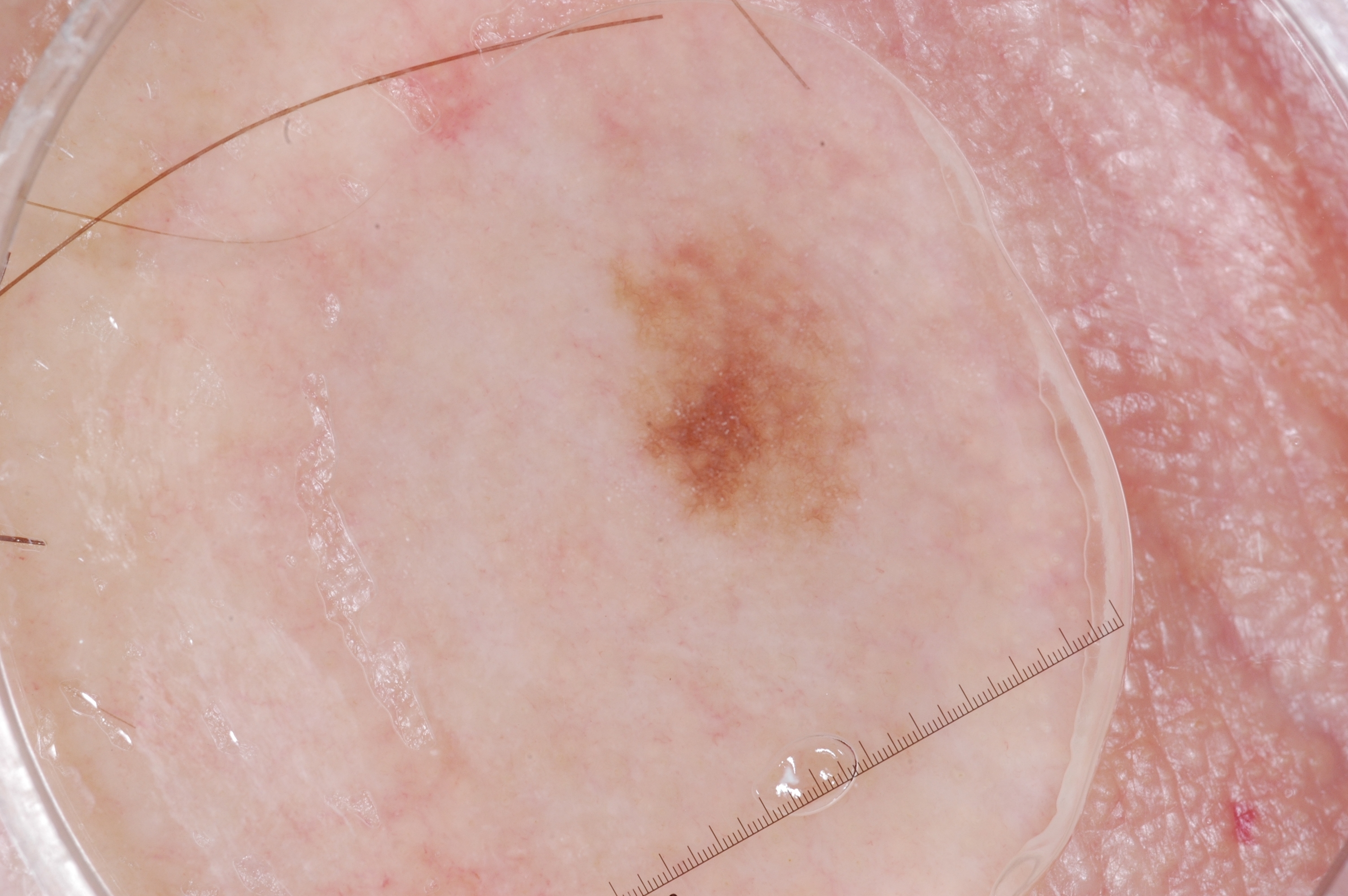Case summary: This is a dermoscopic photograph of a skin lesion. A male subject roughly 60 years of age. Dermoscopic review identifies pigment network. As (left, top, right, bottom), lesion location: <bbox>597, 205, 878, 557</bbox>. A small lesion occupying a minor part of the field. Assessment: Consistent with a melanocytic nevus, a benign skin lesion.